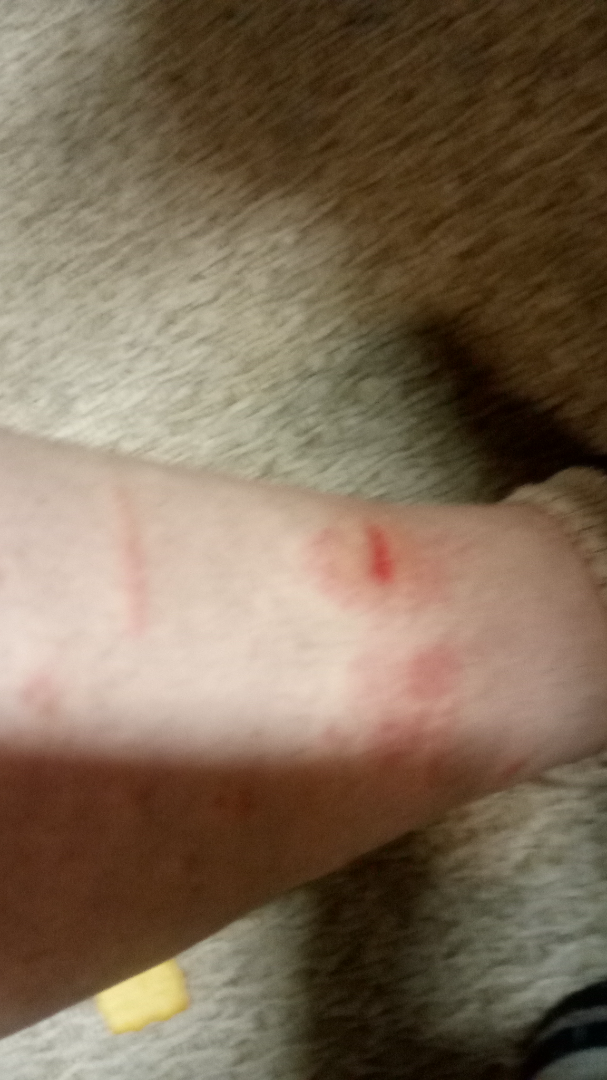Background:
The patient considered this skin that appeared healthy to them. The patient notes bleeding, burning, itching, darkening, enlargement and pain. The patient also reports chills, fatigue and joint pain. Located on the back of the torso, head or neck, leg, arm and back of the hand. The lesion is described as raised or bumpy, flat, fluid-filled and rough or flaky. Reported duration is one to four weeks. Skin tone: self-reported Fitzpatrick phototype III; non-clinician graders estimated Monk Skin Tone 2. A close-up photograph. Female contributor, age 40–49.
Findings:
Reviewed remotely by three dermatologists: most consistent with Allergic Contact Dermatitis.